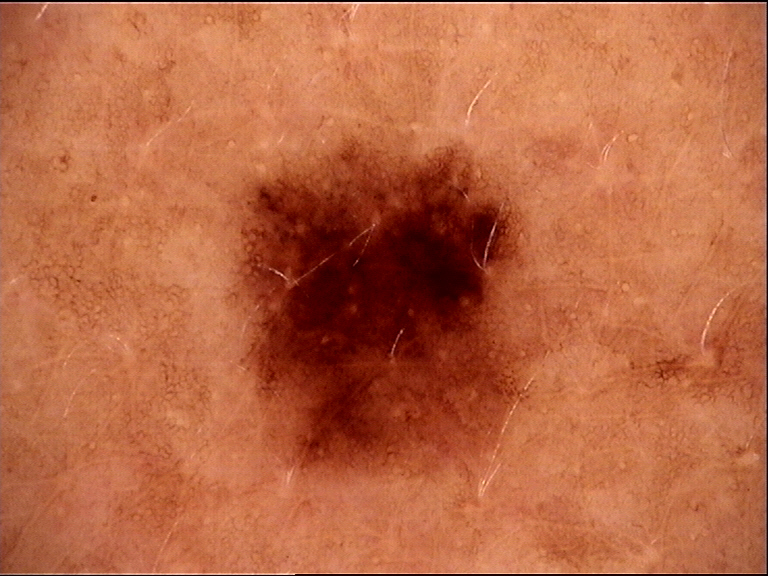The diagnosis was a dysplastic junctional nevus.